Self-categorized by the patient as acne · the contributor is male · symptoms reported: bothersome appearance · the contributor notes the condition has been present for about one day · the lesion involves the head or neck · the photograph is a close-up of the affected area · texture is reported as raised or bumpy.
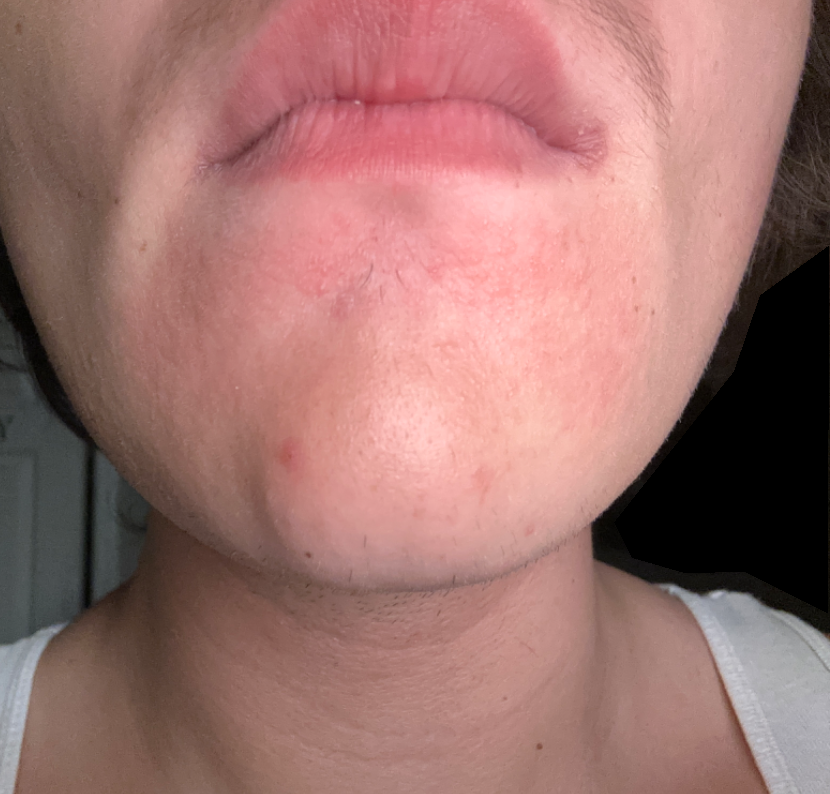Q: What conditions are considered?
A: Perioral Dermatitis, Allergic Contact Dermatitis and Irritant Contact Dermatitis were considered with similar weight